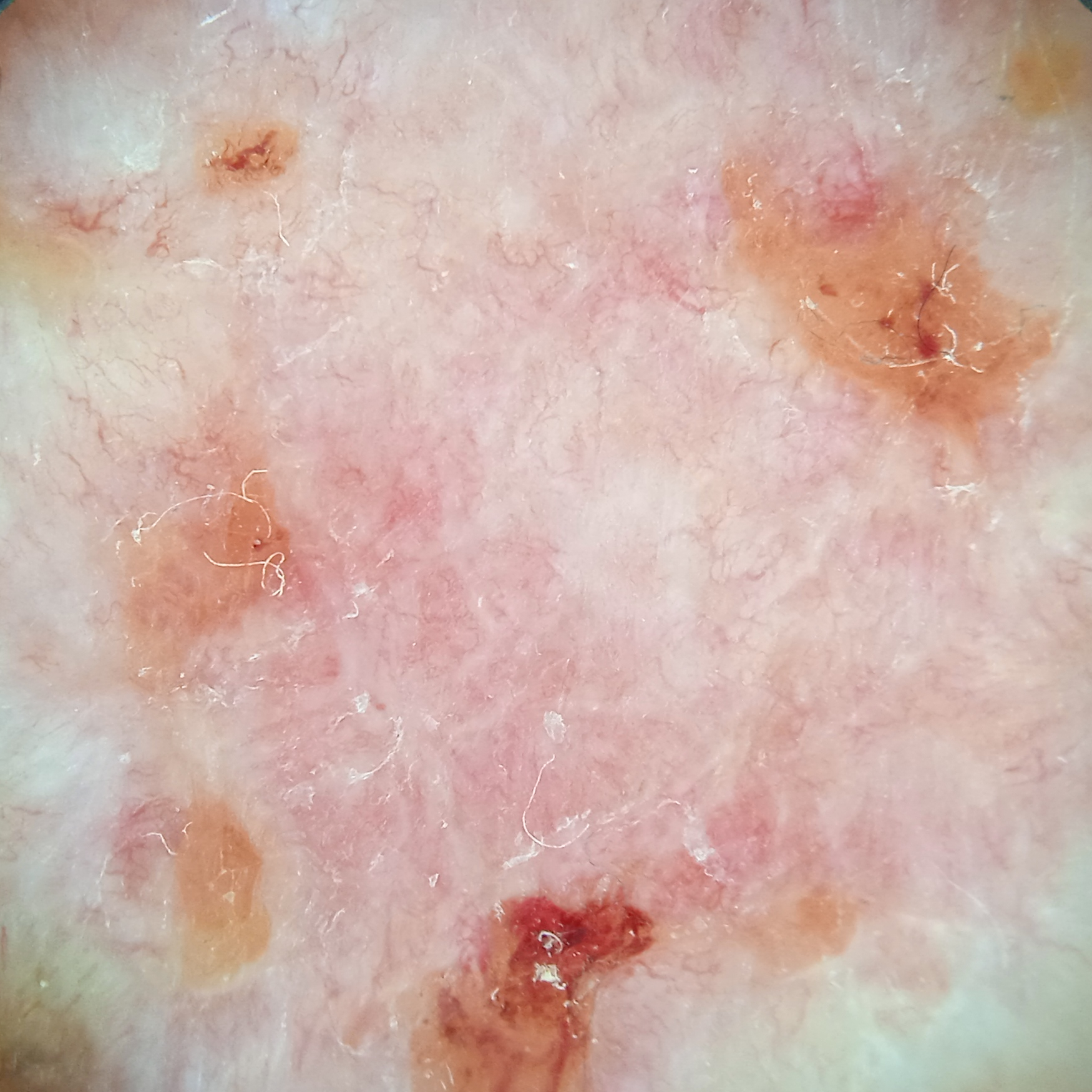* referral context — clinical suspicion of basal cell carcinoma
* modality — dermatoscopic image
* risk factors — a family history of skin cancer, a personal history of cancer, no immunosuppression
* nevus count — few melanocytic nevi overall
* patient — male, 81 years of age
* location — the back
* diagnosis — basal cell carcinoma (biopsy-proven)